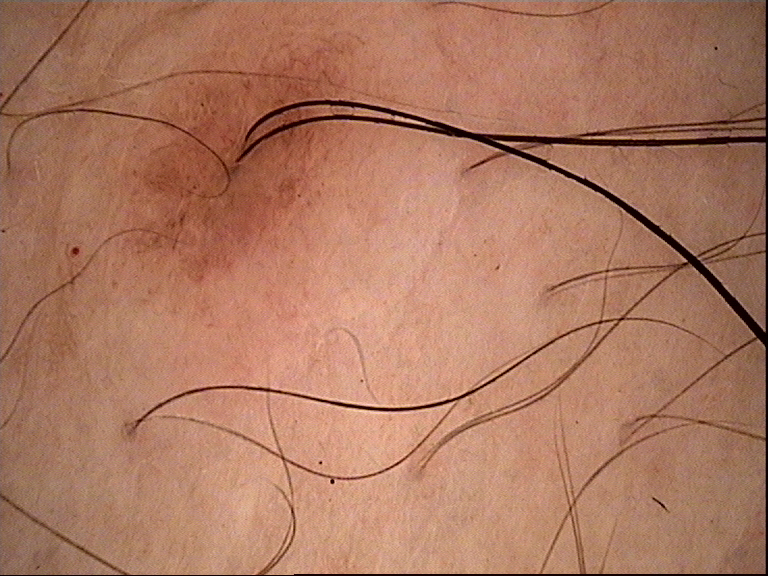Q: What kind of lesion is this?
A: banal
Q: What was the diagnostic impression?
A: dermal nevus (expert consensus)